A female subject in their late 30s · recorded as skin type II · the chart notes alcohol use, prior malignancy (patient or family), and pesticide exposure · a clinical close-up photograph of a skin lesion.
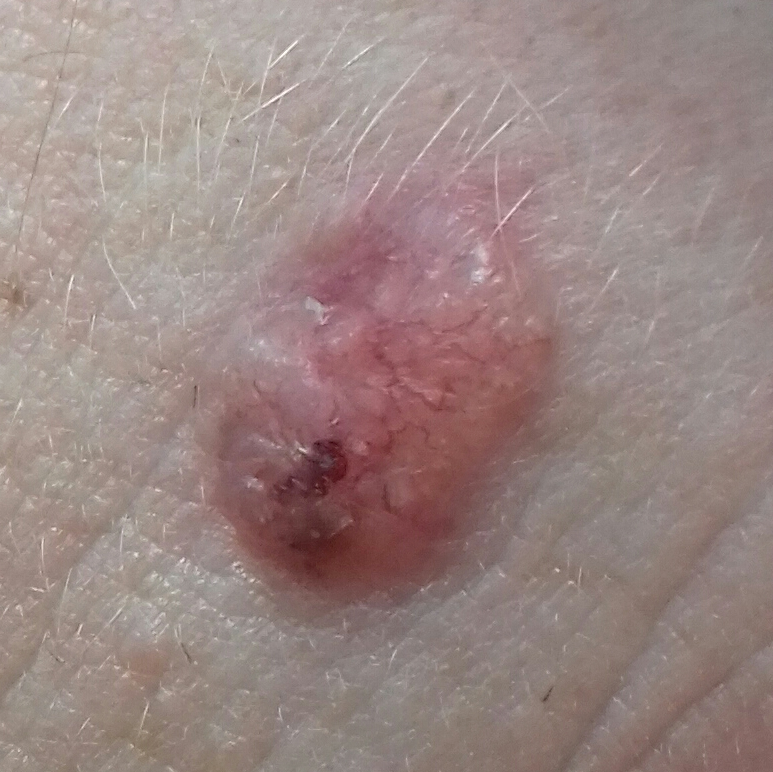{
  "lesion_size": {
    "diameter_1_mm": 13.0,
    "diameter_2_mm": 8.0
  },
  "diagnosis": {
    "name": "basal cell carcinoma",
    "code": "BCC",
    "malignancy": "malignant",
    "confirmation": "histopathology"
  }
}